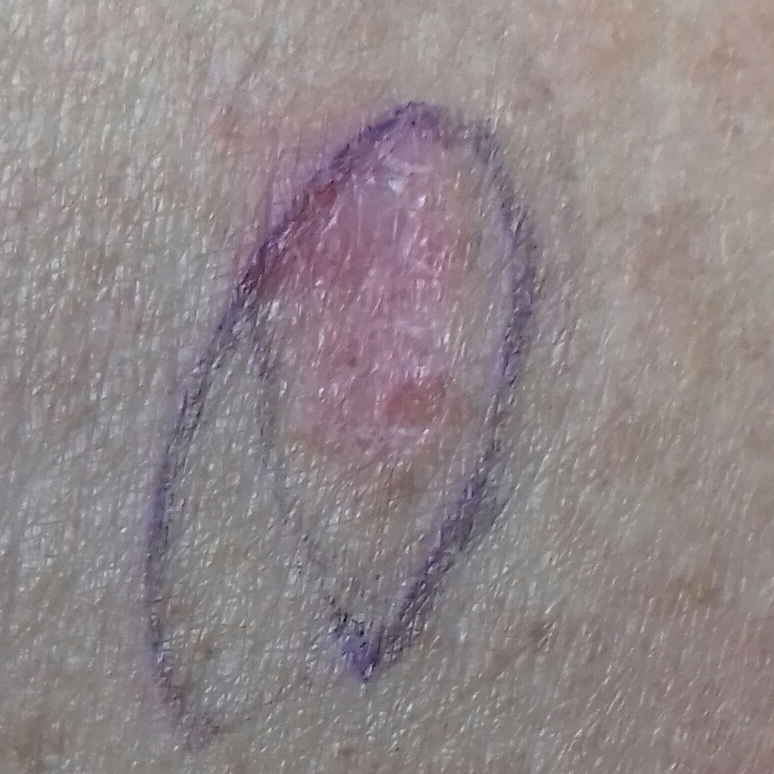Case summary:
Recorded as Fitzpatrick skin type II. By history, pesticide exposure, prior malignancy (patient or family), and prior skin cancer (patient or family). A smartphone photograph of a skin lesion. A female patient 53 years of age. The lesion is located on the back. The lesion is roughly 100 by 70 mm. By the patient's account, the lesion has not bled.
Diagnosis:
Histopathological examination showed a skin cancer — a basal cell carcinoma.